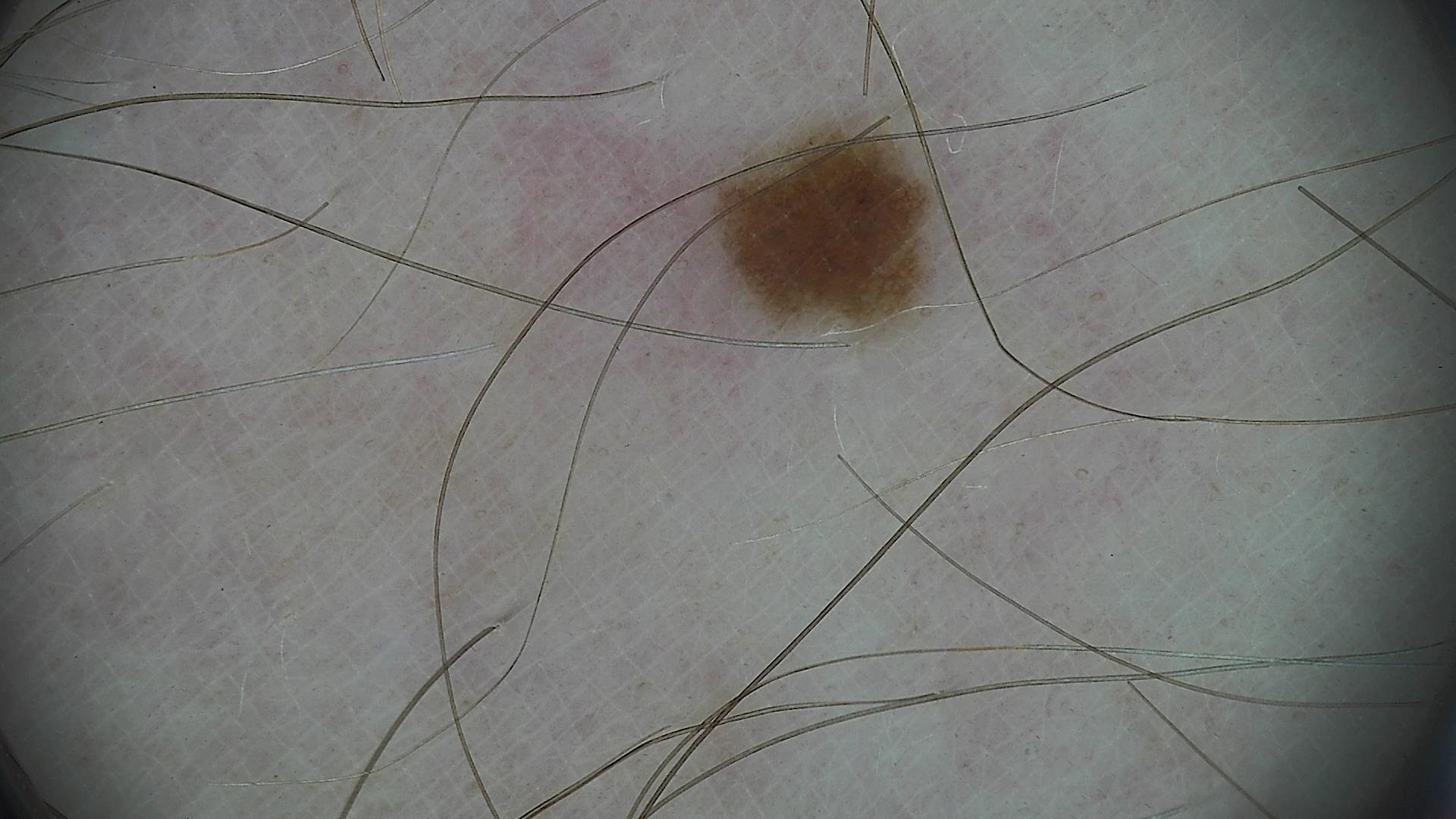Diagnosed as a junctional nevus.